The photo was captured at an angle: 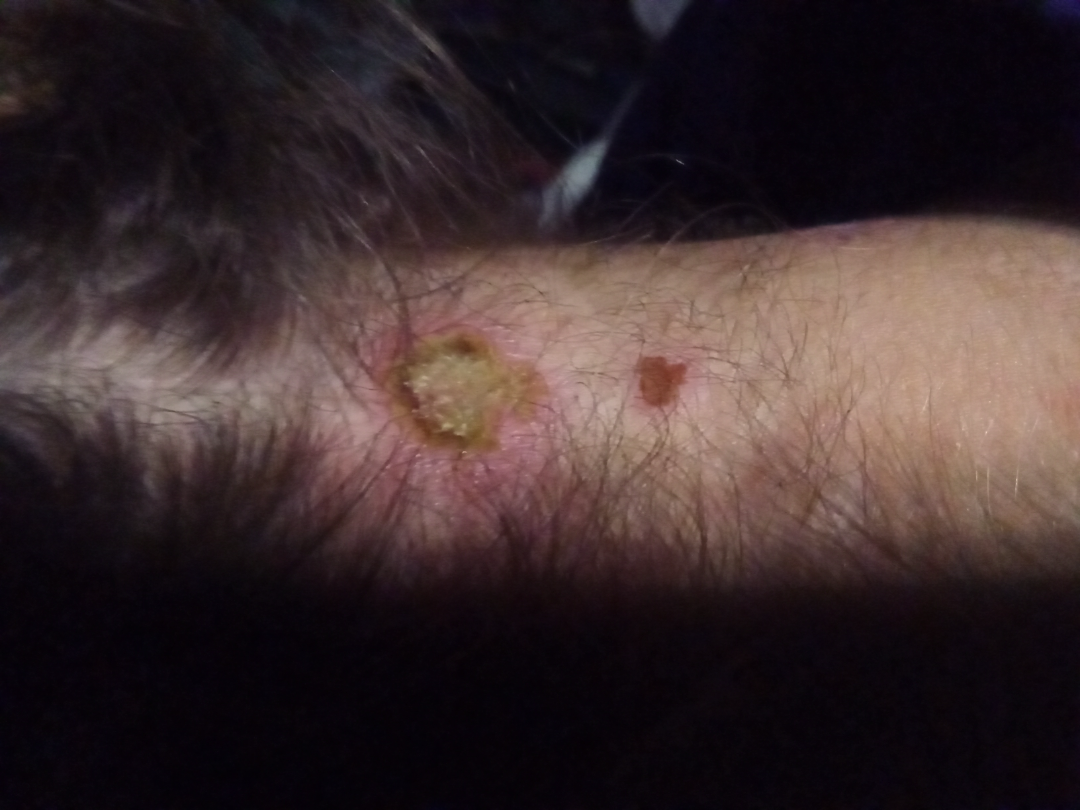No differential diagnosis could be assigned on photographic review.